Dermoscopy of a skin lesion · the patient says their skin reddens with sun exposure · imaged for a research study, with no referral diagnosis recorded · a male patient age 62:
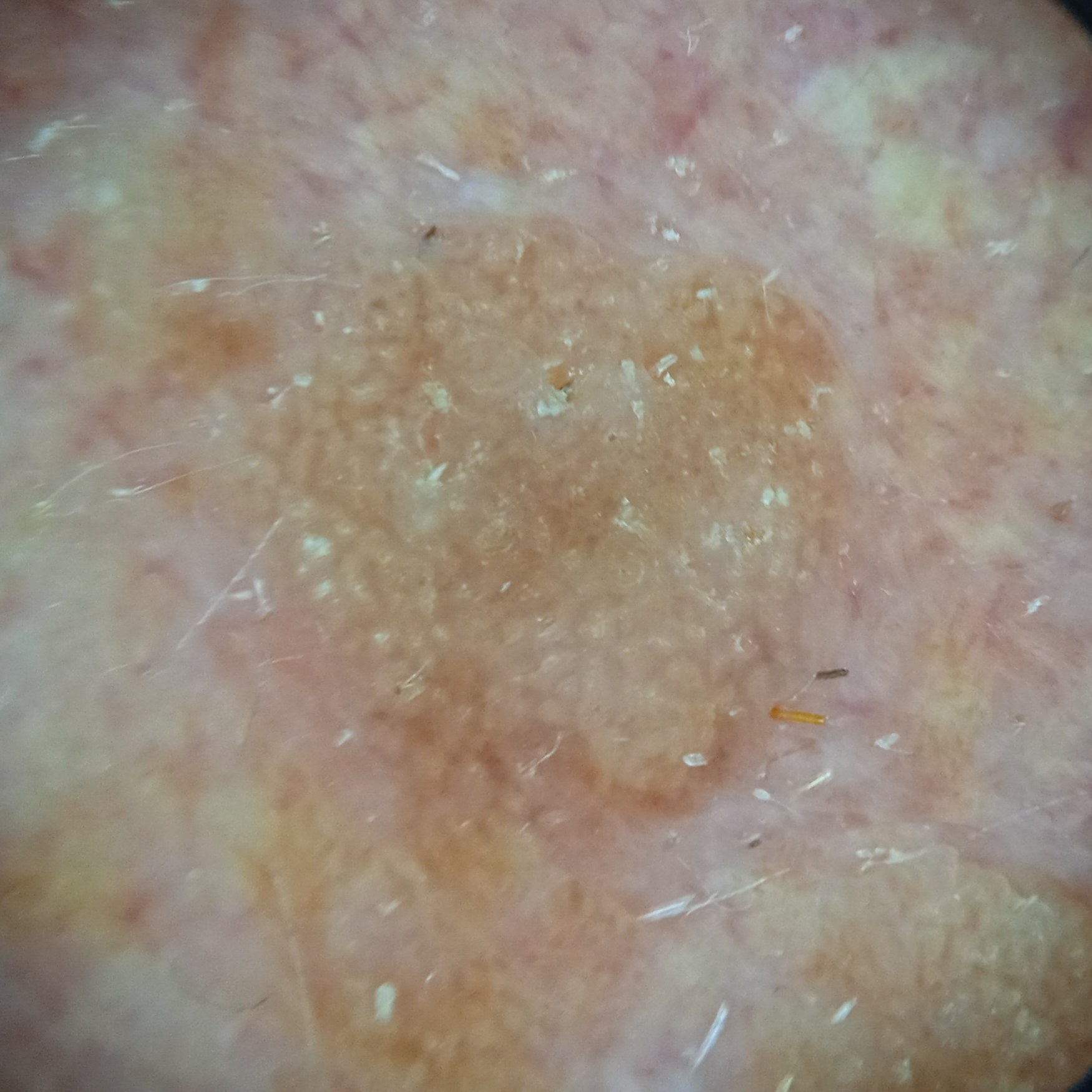The diagnostic impression was a seborrheic keratosis.